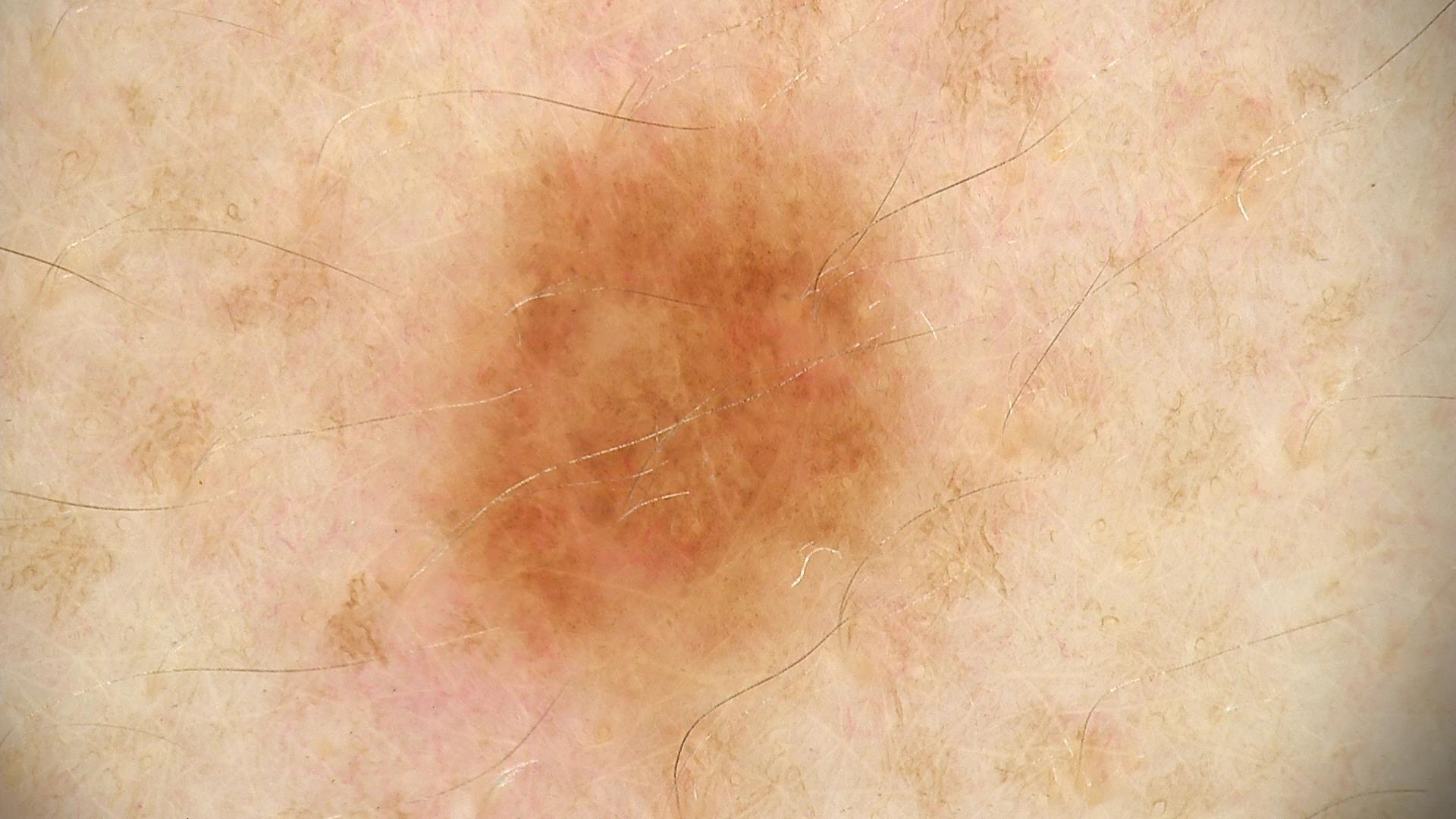  image: dermatoscopy
  diagnosis:
    name: dysplastic junctional nevus
    code: jd
    malignancy: benign
    super_class: melanocytic
    confirmation: expert consensus